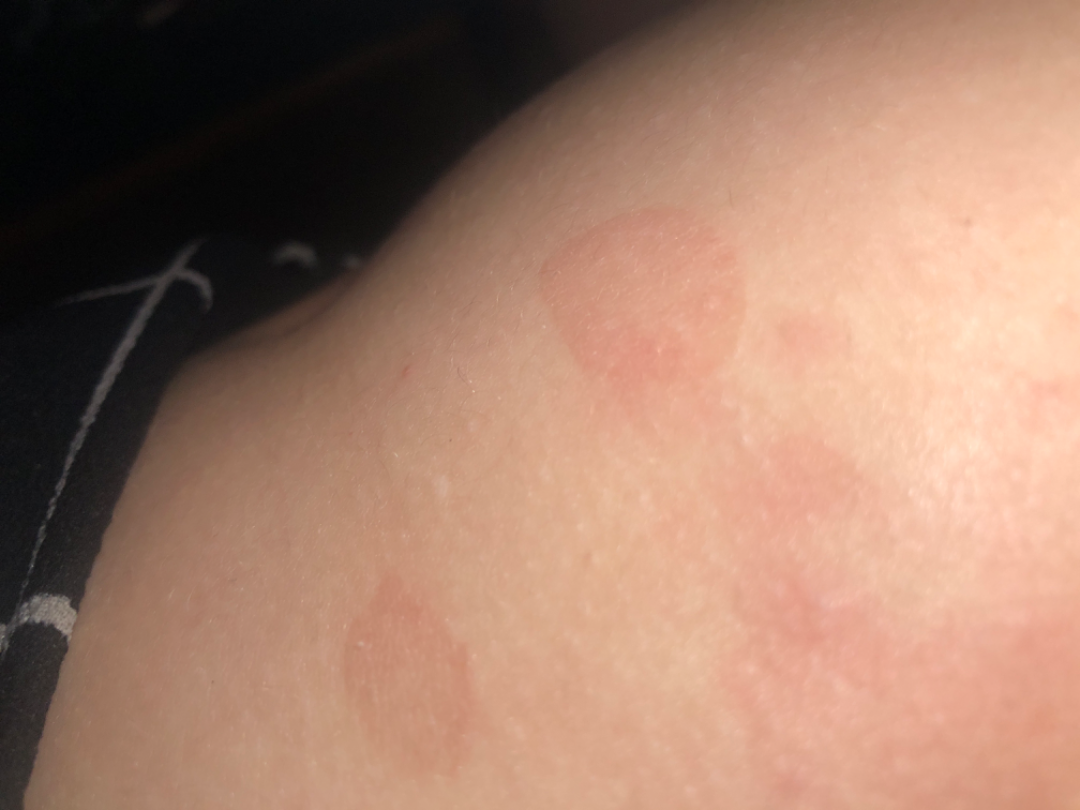On photographic review by a dermatologist, Parapsoriasis, Syphilis and Seborrheic Dermatitis were each considered, in no particular order.